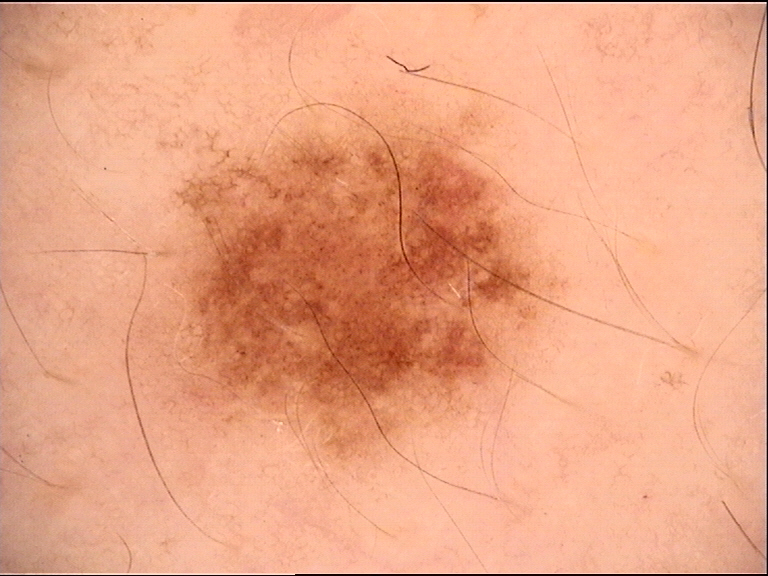Case:
• diagnosis · dysplastic junctional nevus (expert consensus)